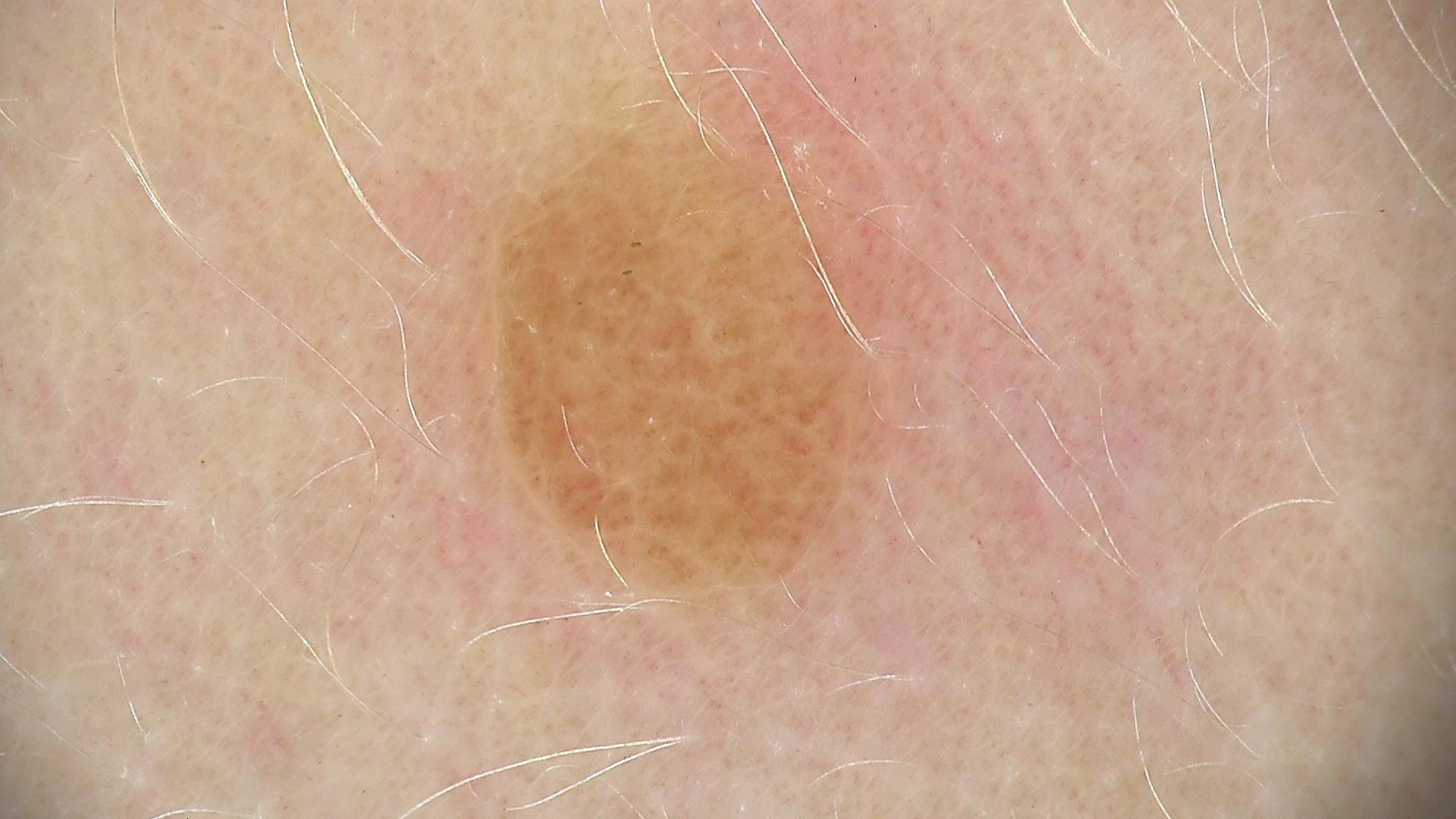label — compound nevus (expert consensus).